A female subject, aged 68 to 72; a dermoscopy image of a single skin lesion — 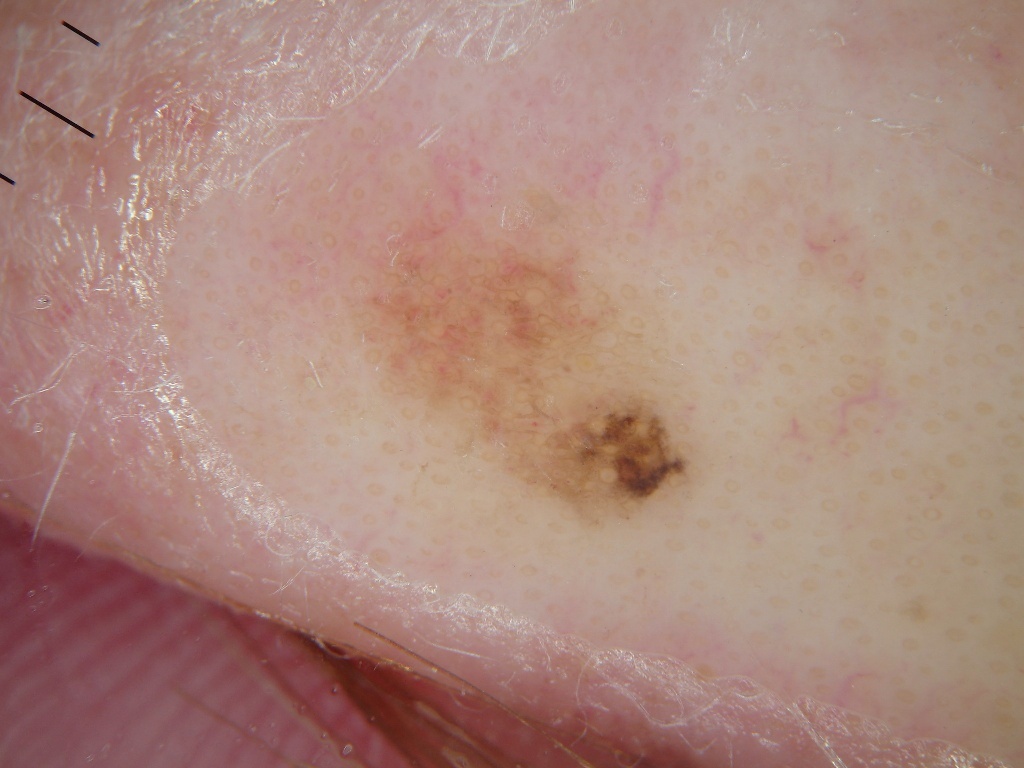Q: Where is the lesion located?
A: x1=350, y1=189, x2=702, y2=531
Q: Lesion extent?
A: ~8% of the field
Q: Which dermoscopic features are absent?
A: milia-like cysts, globules, pigment network, streaks, and negative network
Q: What is the diagnosis?
A: a melanocytic nevus